A dermoscopic close-up of a skin lesion.
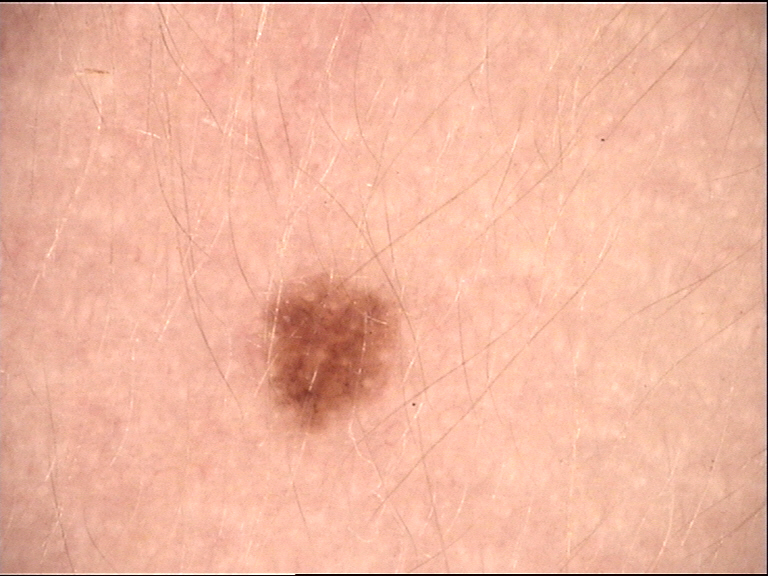diagnostic label = junctional nevus (expert consensus).